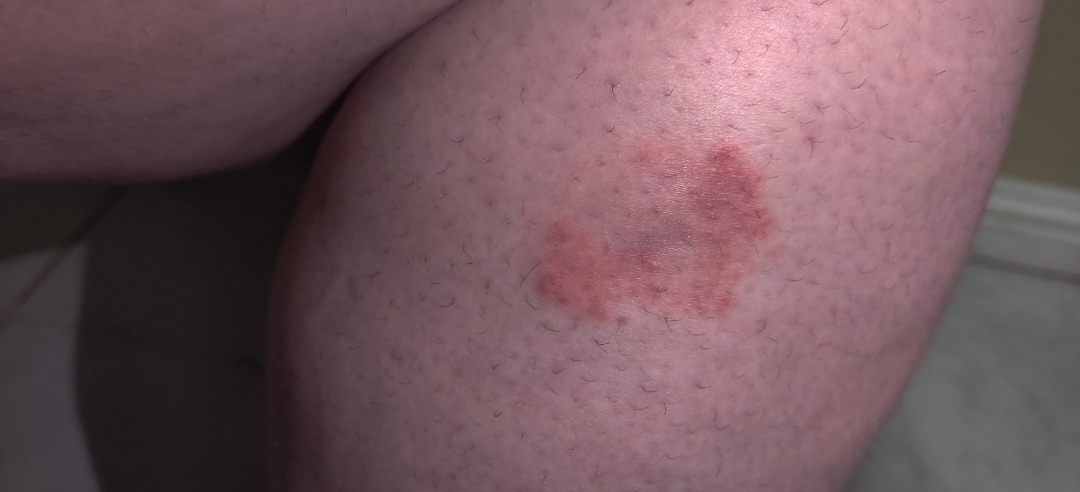The case was indeterminate on photographic review. Skin tone: non-clinician graders estimated a Monk Skin Tone of 2. Reported lesion symptoms include itching, enlargement and bothersome appearance. This is a close-up image. The leg is involved. The patient reports the condition has been present for one to three months. The lesion is described as rough or flaky.